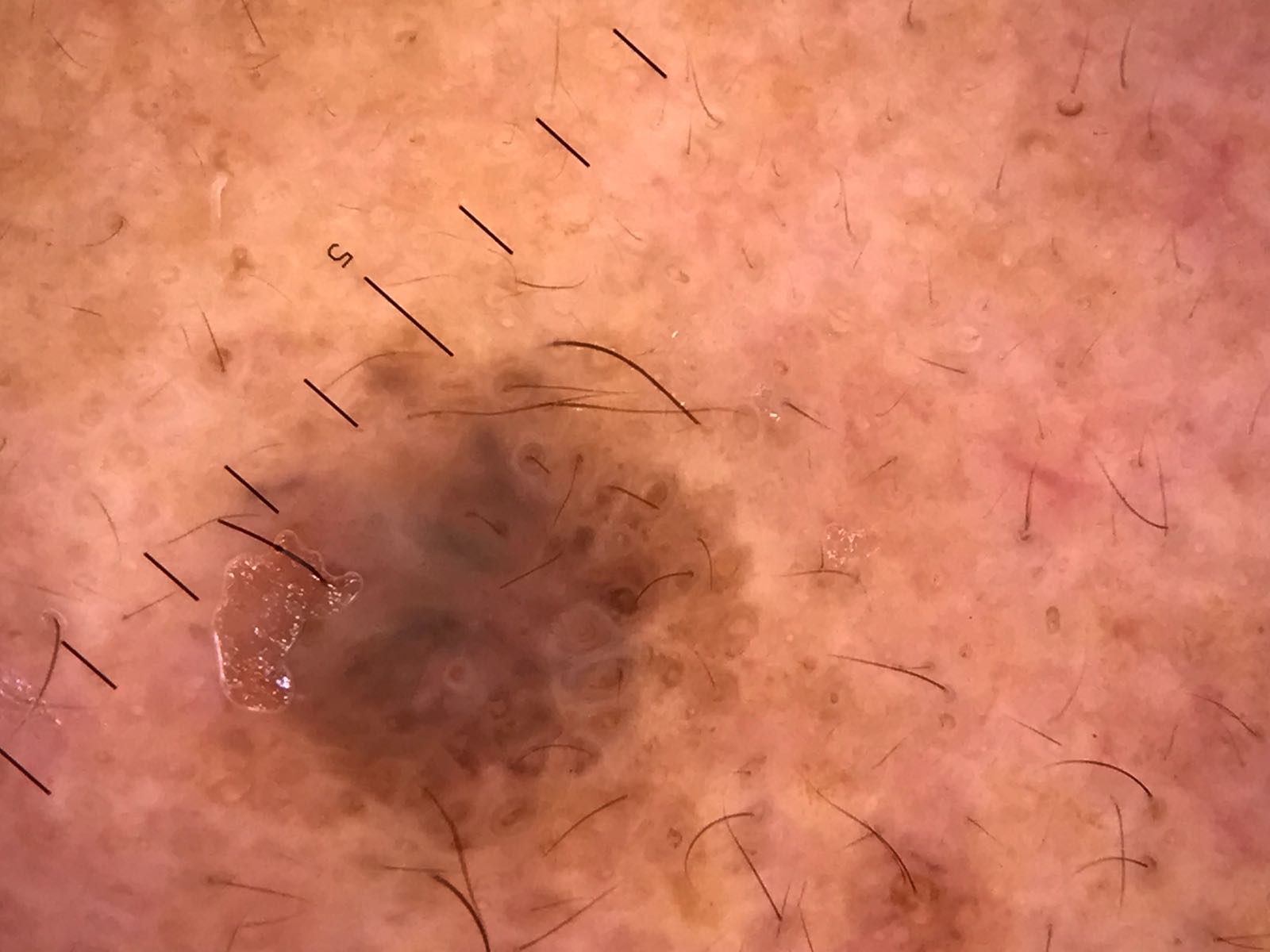A skin lesion imaged with a dermatoscope.
The diagnostic label was a keratinocytic lesion — a seborrheic keratosis.